A smartphone photograph of a skin lesion; a male subject in their 60s; recorded as FST II; by history, pesticide exposure, alcohol use, and tobacco use.
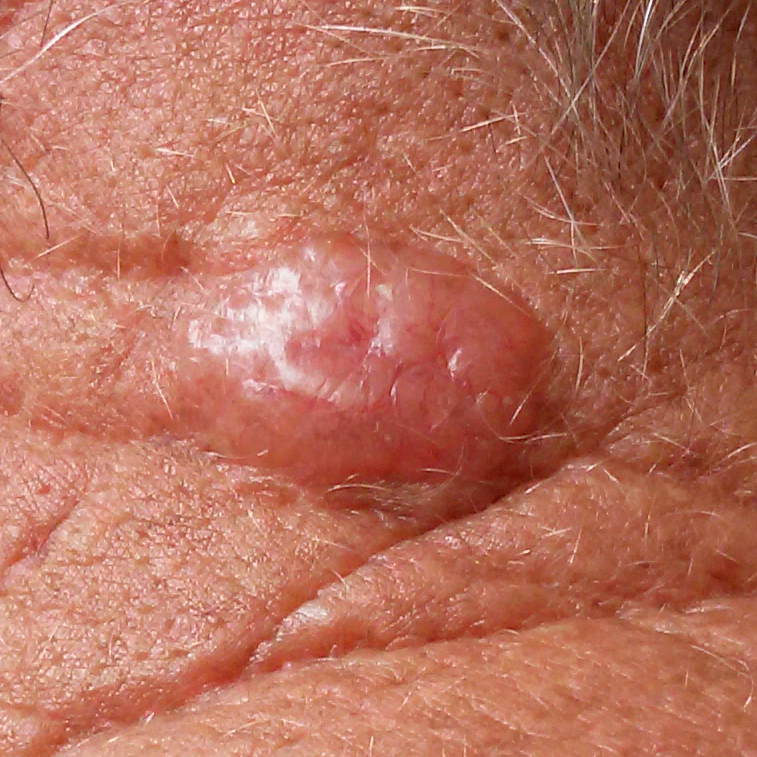Q: Where on the body is the lesion?
A: the neck
Q: How large is the lesion?
A: 14 × 8 mm
Q: What does the patient describe?
A: bleeding, elevation, growth
Q: What is the diagnosis?
A: basal cell carcinoma (biopsy-proven)